Close-up view.
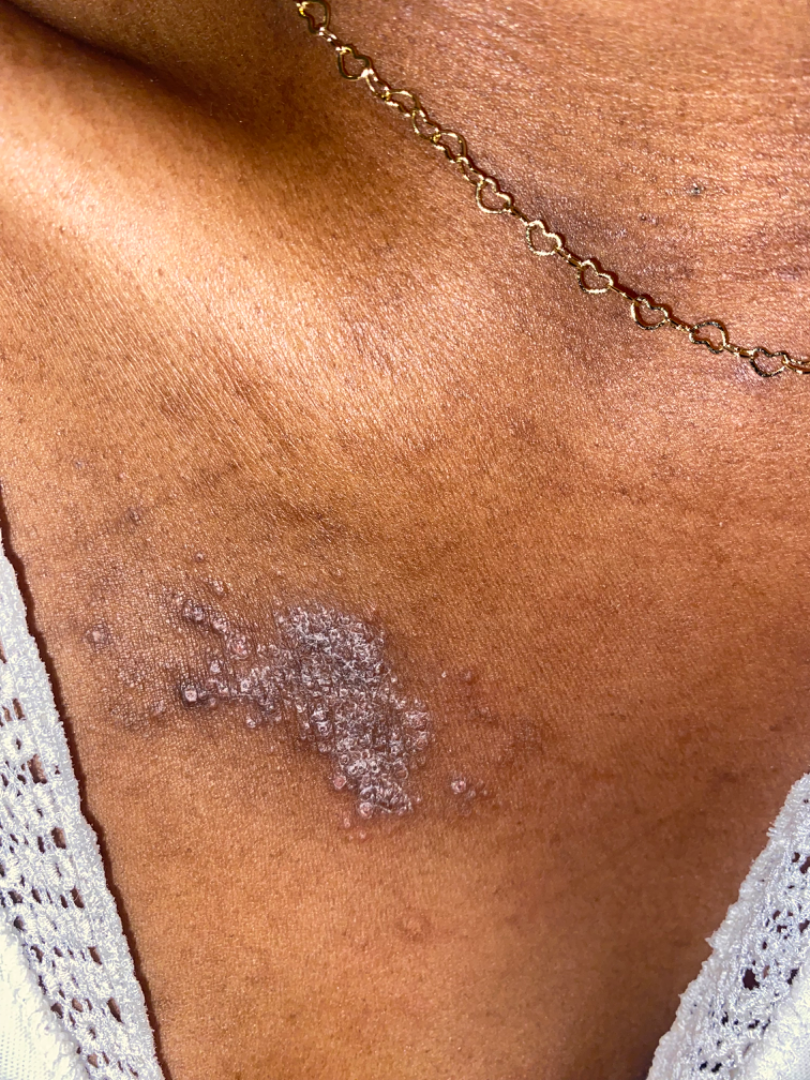Self-categorized by the patient as a rash. Texture is reported as raised or bumpy. On remote review of the image: Lichen planus/lichenoid eruption and Chronic dermatitis, NOS were each considered, in no particular order.